By history, pesticide exposure and prior malignancy (patient or family) · the patient is FST II: 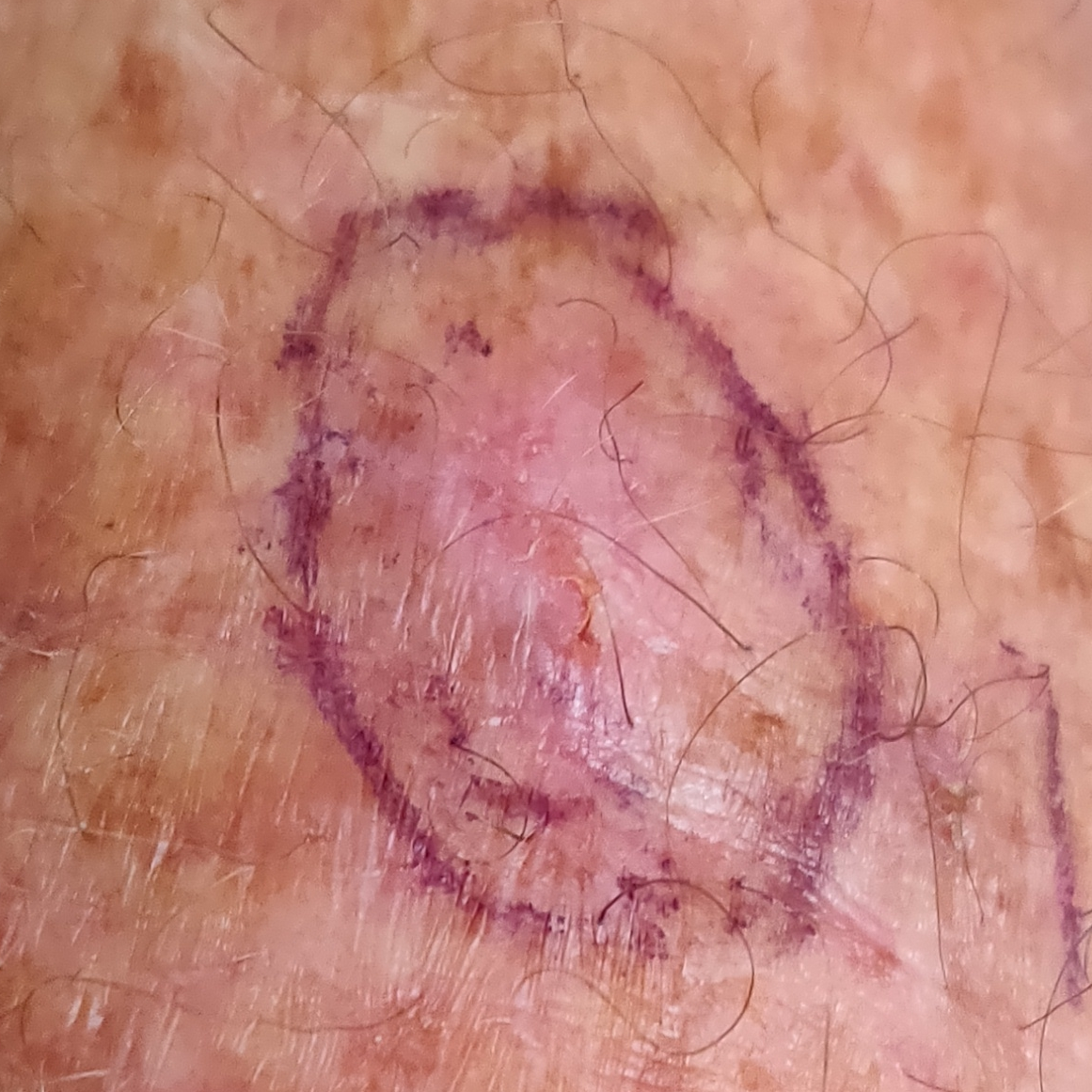Measuring about 11 × 7 mm. Histopathological examination showed a skin cancer — a squamous cell carcinoma.